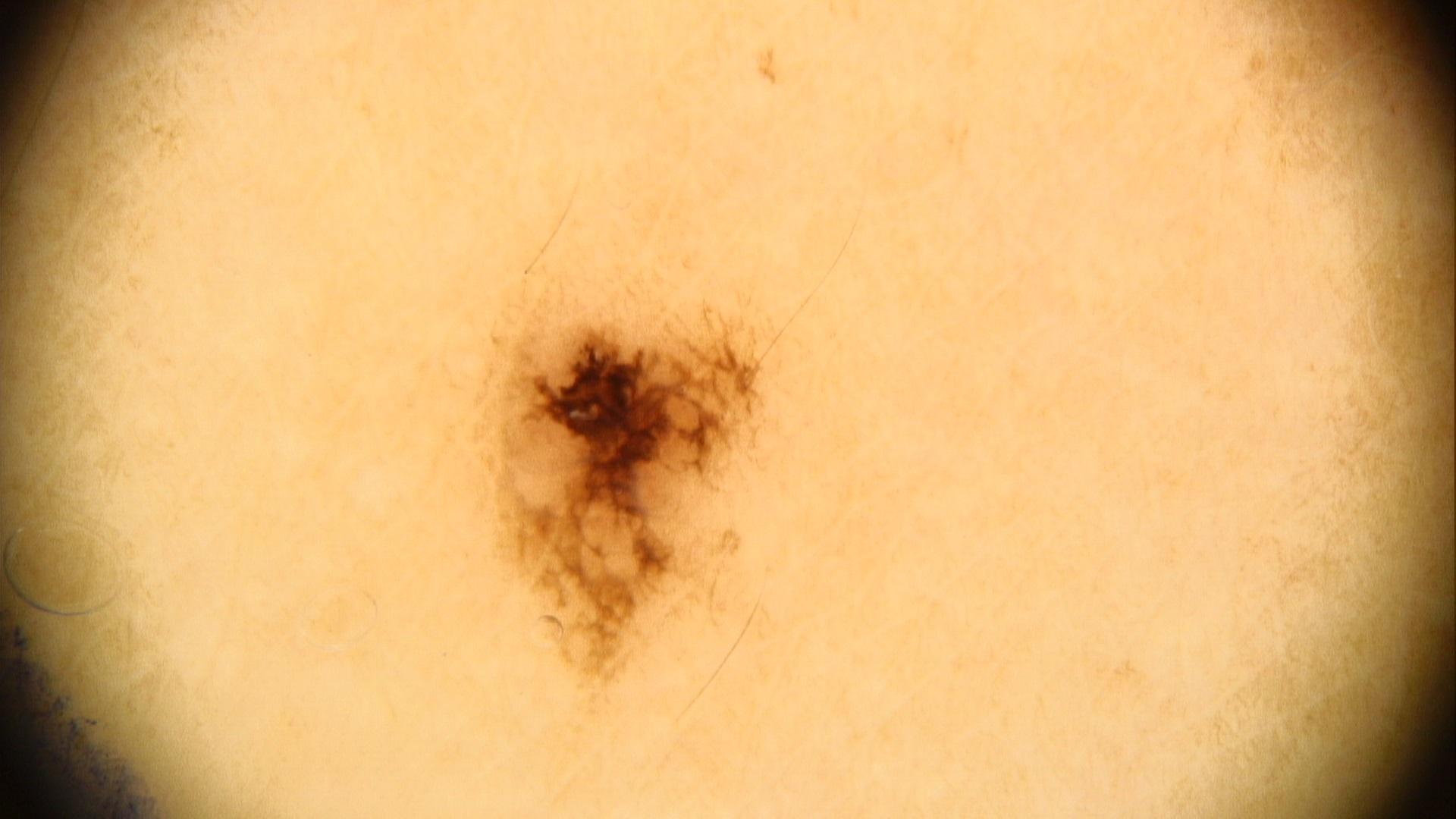Case:
• modality — contact-polarized dermoscopy
• subject — female, roughly 40 years of age
• risk factors — no prior melanoma and no melanoma in first-degree relatives
• location — a lower extremity
• diagnosis — Nevus (biopsy-proven)